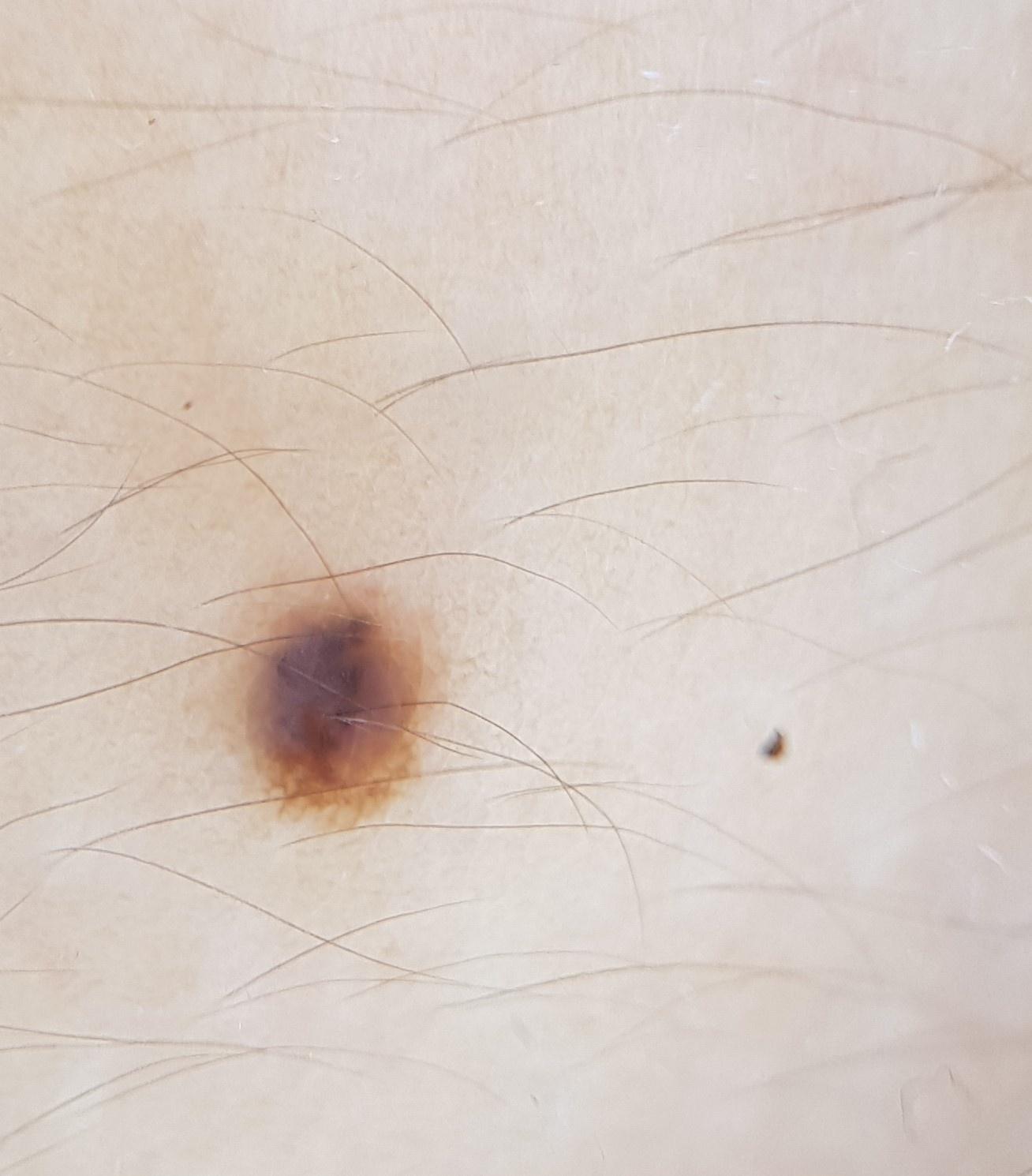On biopsy, the diagnosis was a nevus.